The affected area is the back of the hand and back of the torso. This is a close-up image.
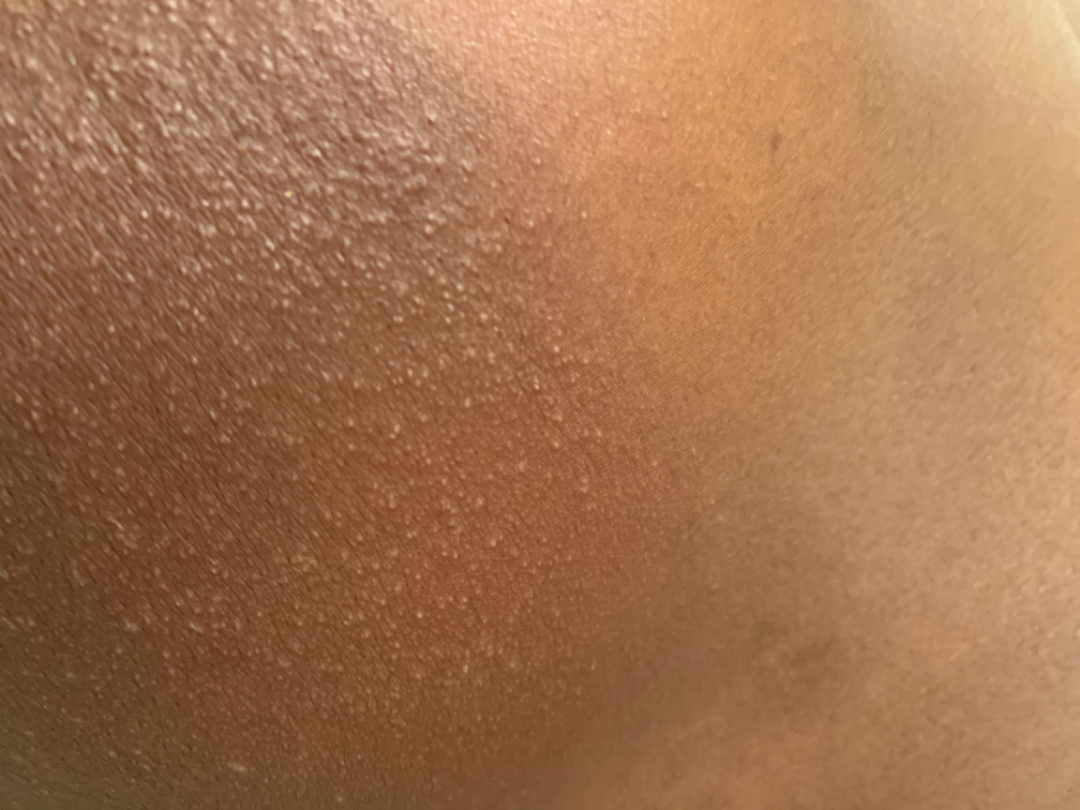Findings: The condition could not be reliably identified from the image.